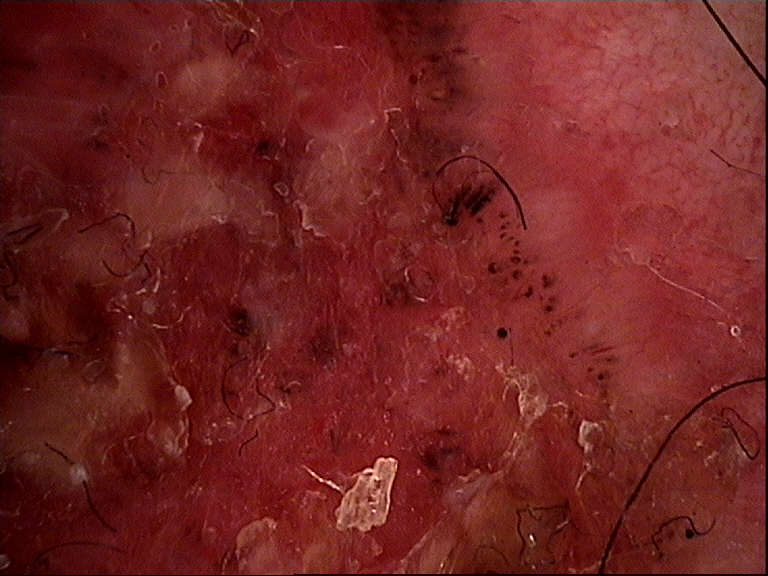The morphology is that of a keratinocytic lesion. Biopsy-confirmed as a malignancy — a basal cell carcinoma.